Male contributor, age 40–49. A close-up photograph. The affected area is the back of the torso, arm and leg.
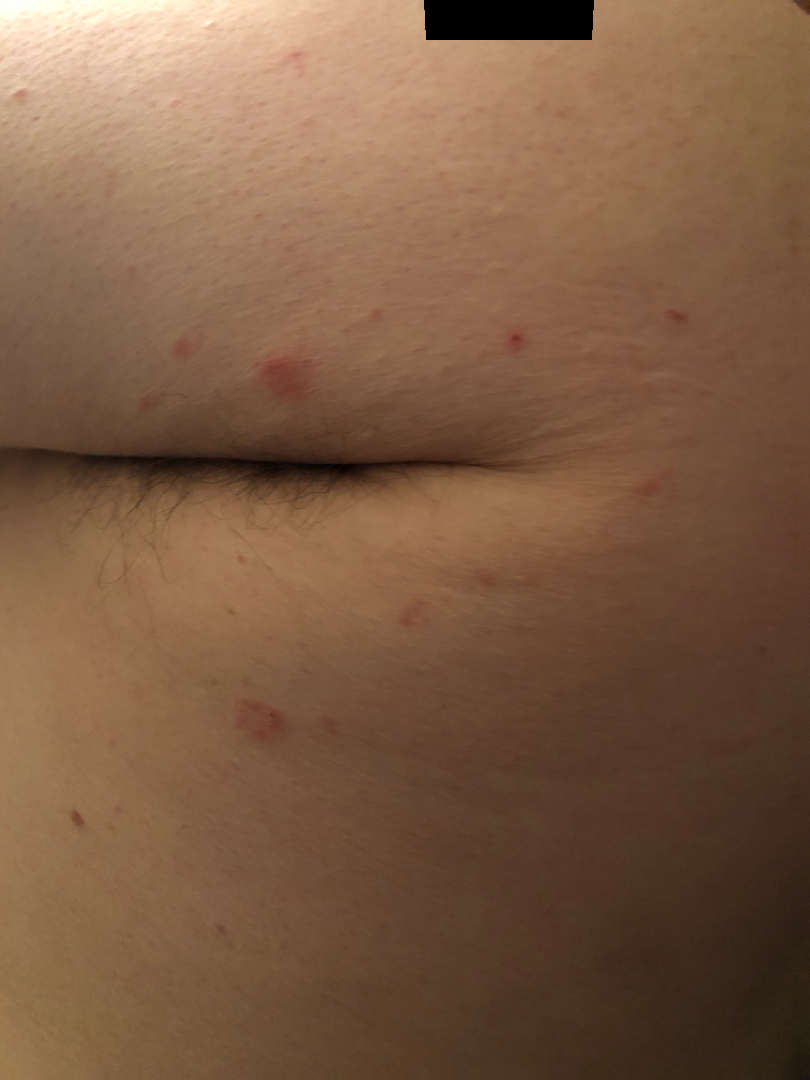The case was indeterminate on photographic review.